Dermoscopy of a skin lesion. A female subject:
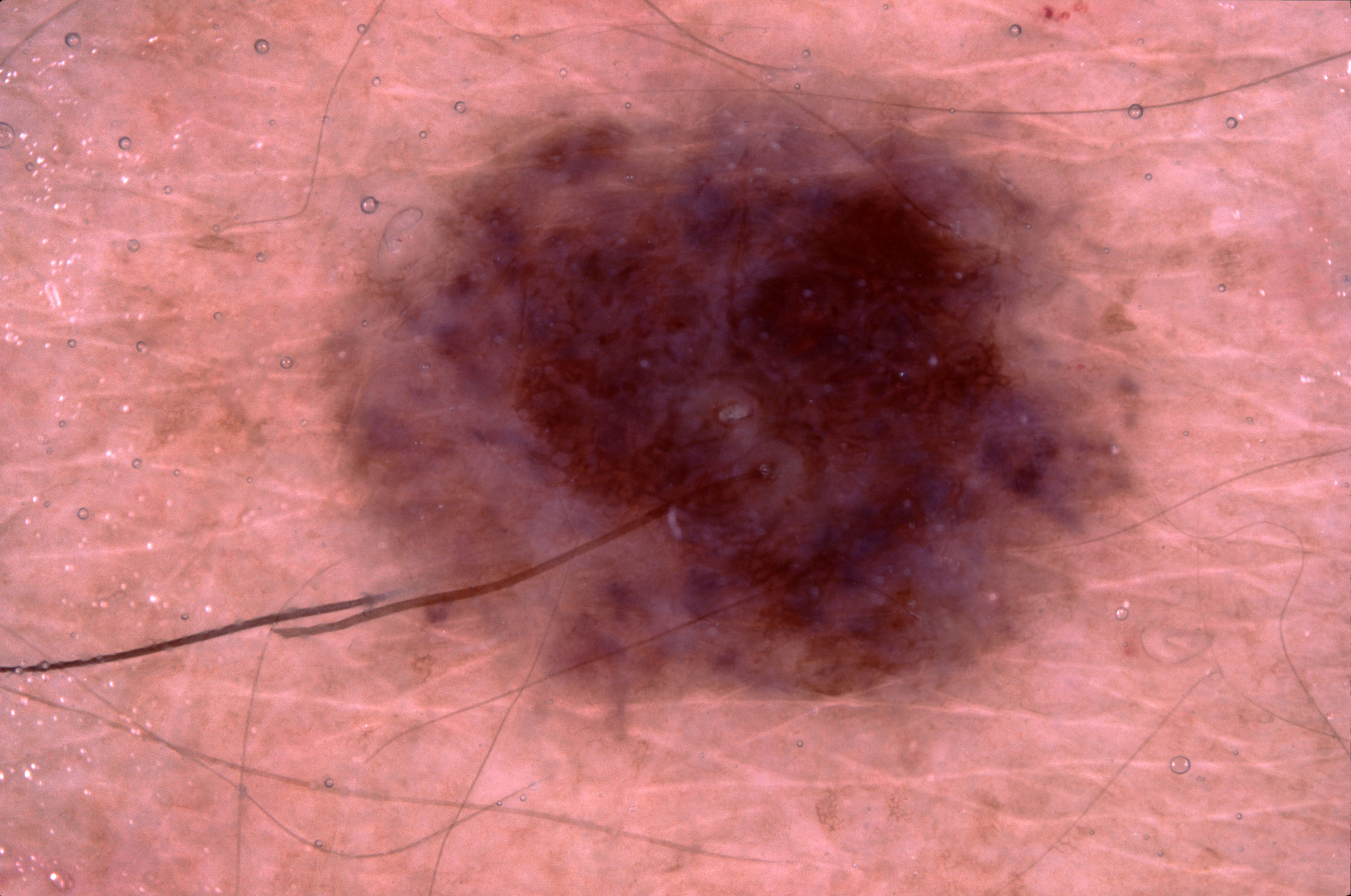Dermoscopic review identifies pigment network, with no negative network, milia-like cysts, or streaks.
As (left, top, right, bottom), lesion location: 282/14/1195/760.
Expert review diagnosed this as a melanocytic nevus, a benign skin lesion.